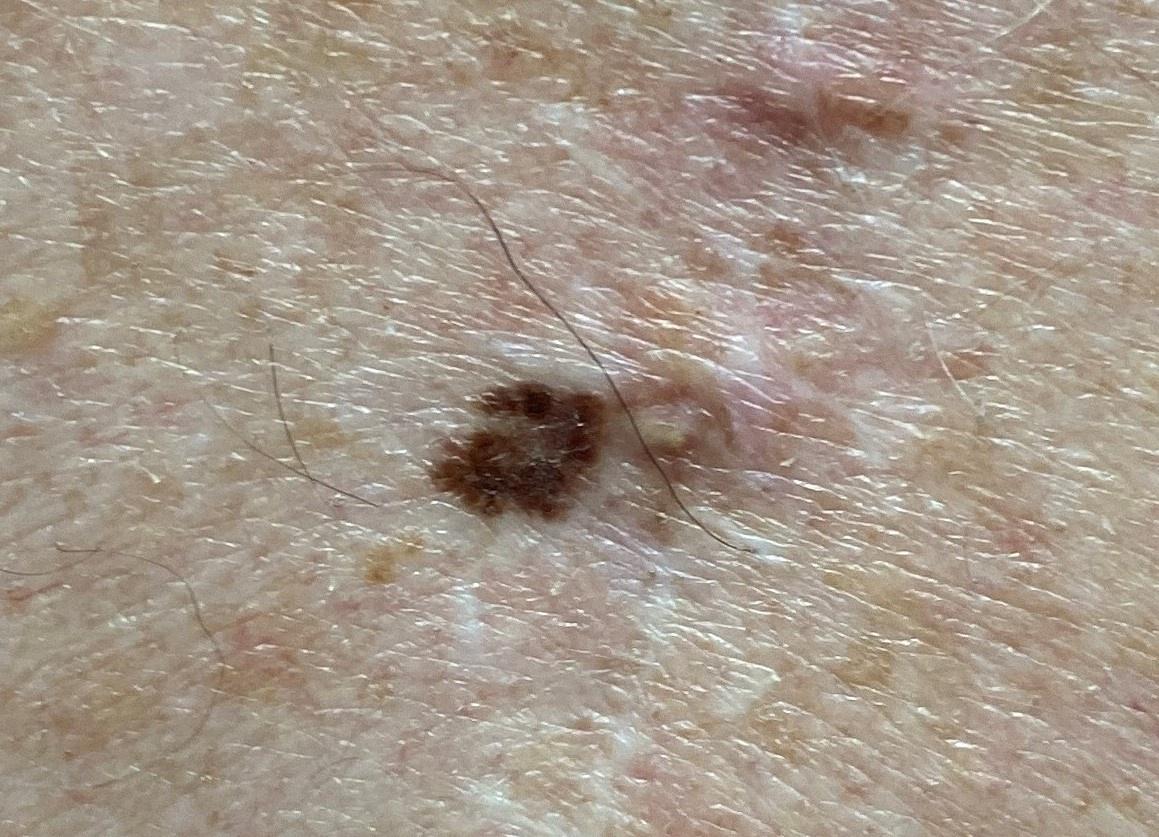A clinical overview photograph of a skin lesion. Recorded as Fitzpatrick II. A male subject about 80 years old. The lesion was found on the trunk, specifically the posterior trunk. Histopathologically confirmed as a lesion of melanocytic lineage — a nevus.